The patient considered this a rash · the back of the torso, front of the torso and head or neck are involved · skin tone: Fitzpatrick phototype II; lay graders estimated a Monk Skin Tone of 2 · the patient reported no systemic symptoms · the contributor reports bothersome appearance, itching and burning · a close-up photograph · the contributor is female · the lesion is described as raised or bumpy and rough or flaky — 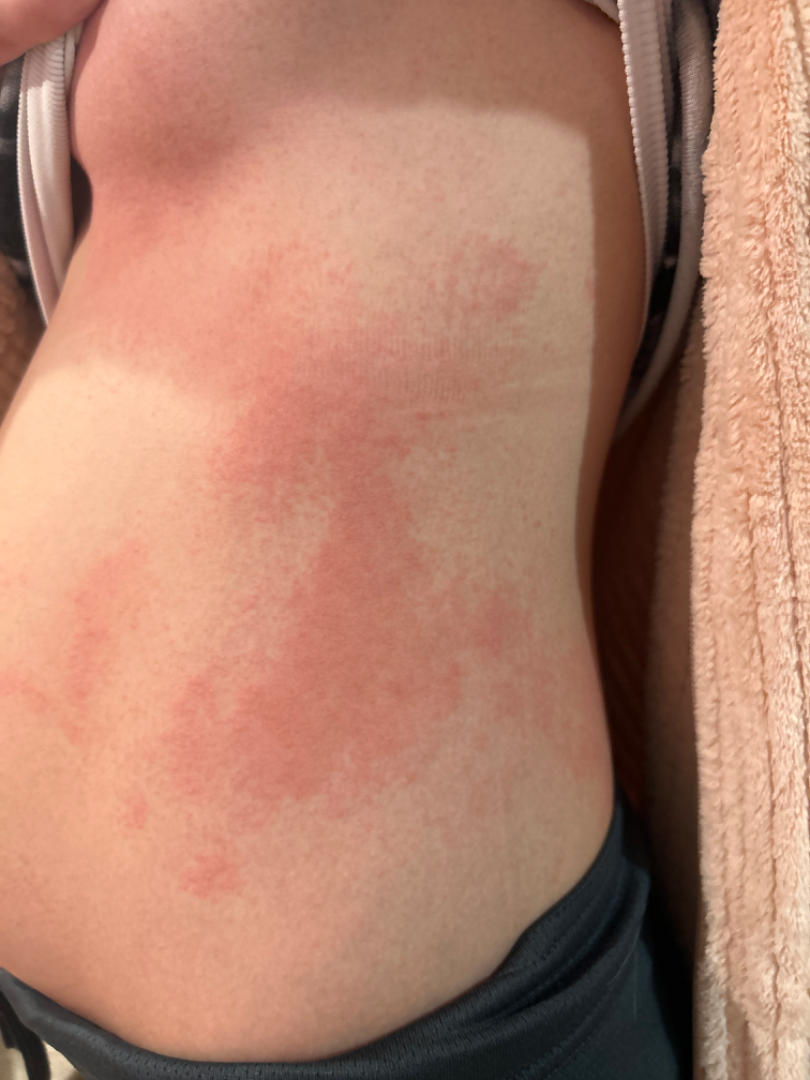Case summary:
* clinical impression: the favored diagnosis is Hypersensitivity; also raised was Eczema